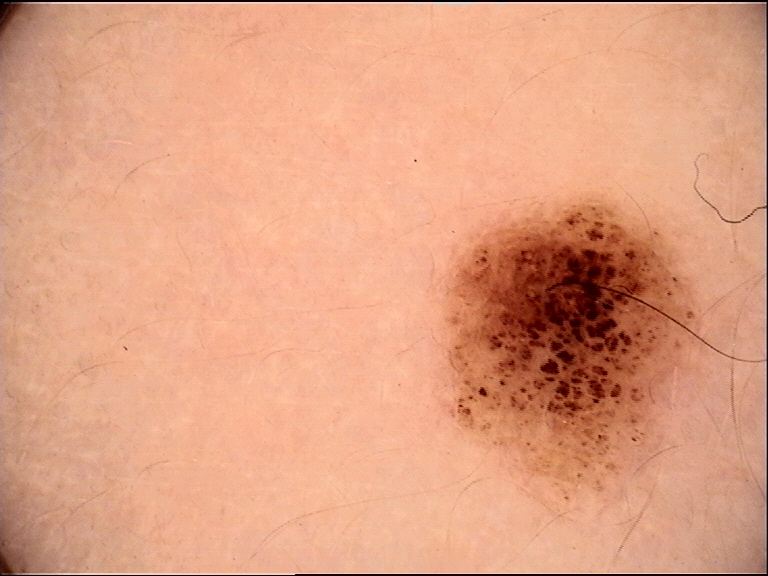label: dysplastic compound nevus (expert consensus).